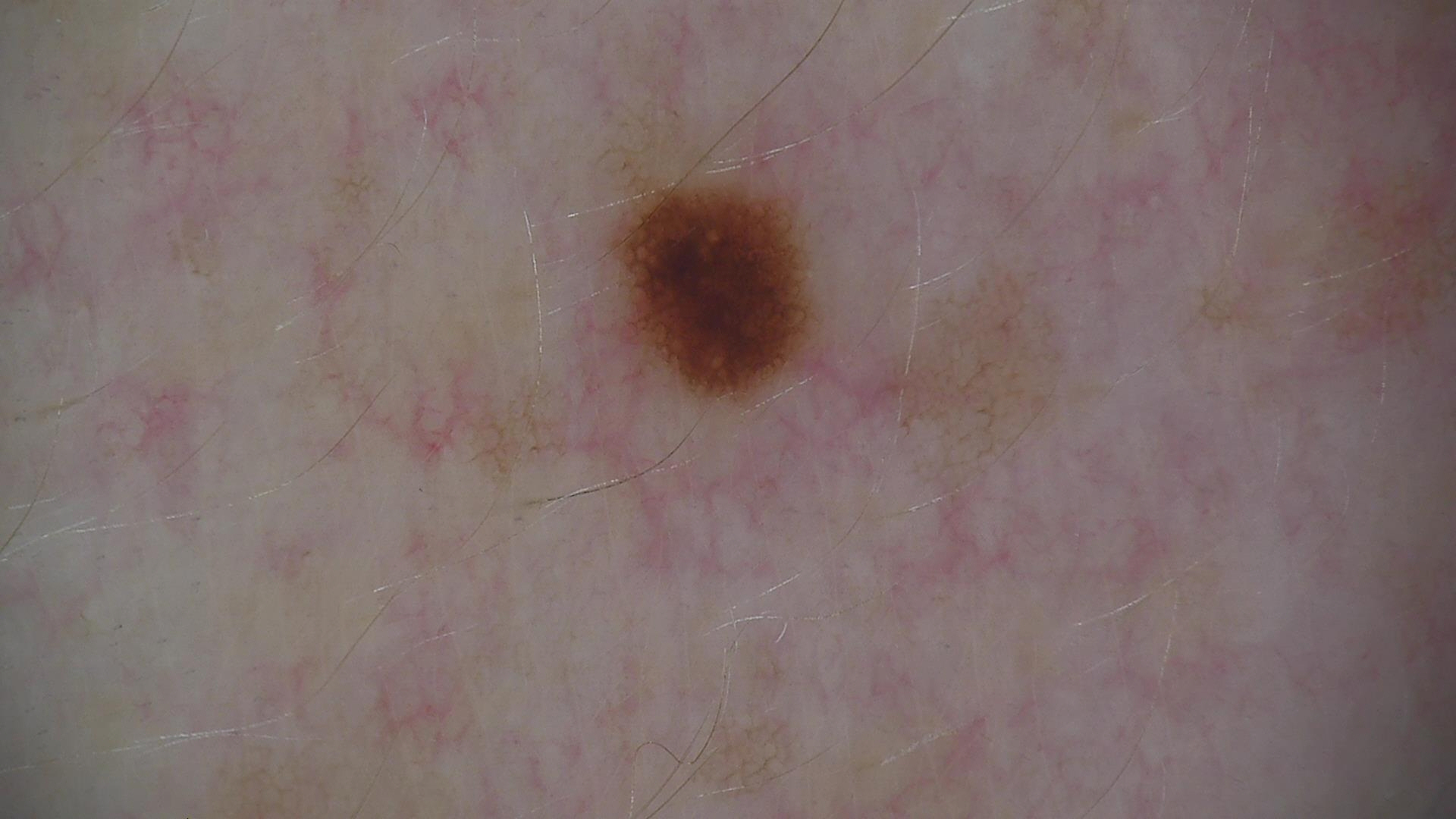The diagnosis was a junctional nevus.